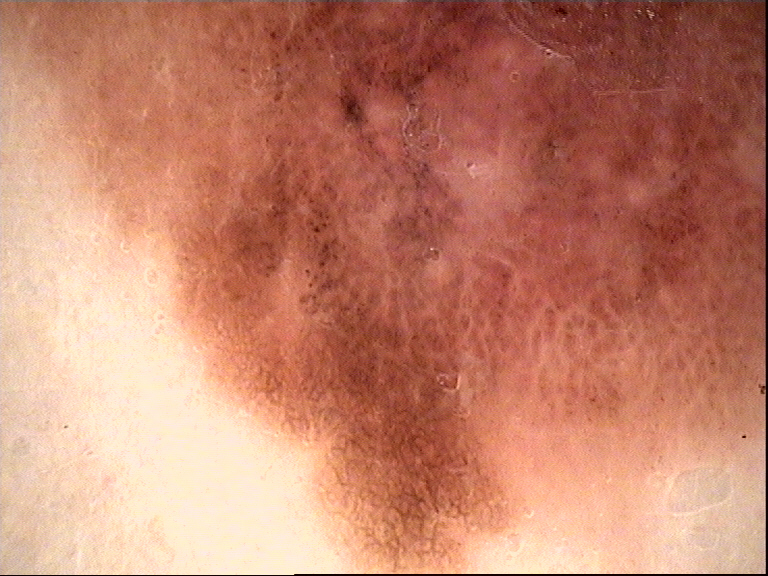A dermoscopic image of a skin lesion.
Biopsy-confirmed as an acral lentiginous melanoma.